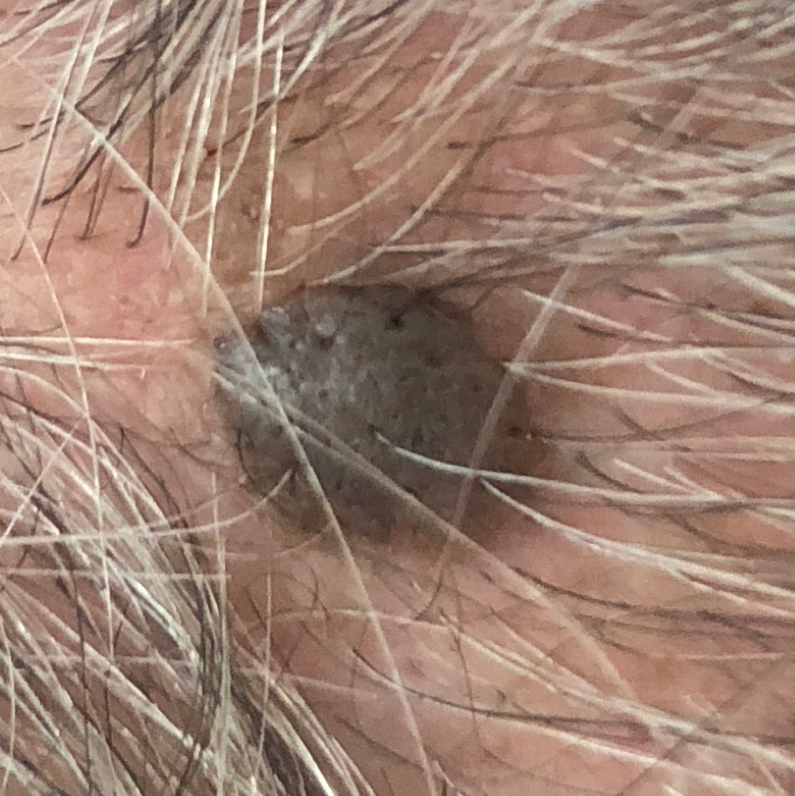| key | value |
|---|---|
| modality | clinical photograph |
| subject | in their 70s |
| anatomic site | the scalp |
| symptoms | growth, elevation, itching / no change in appearance, no bleeding |
| assessment | seborrheic keratosis (clinical consensus) |